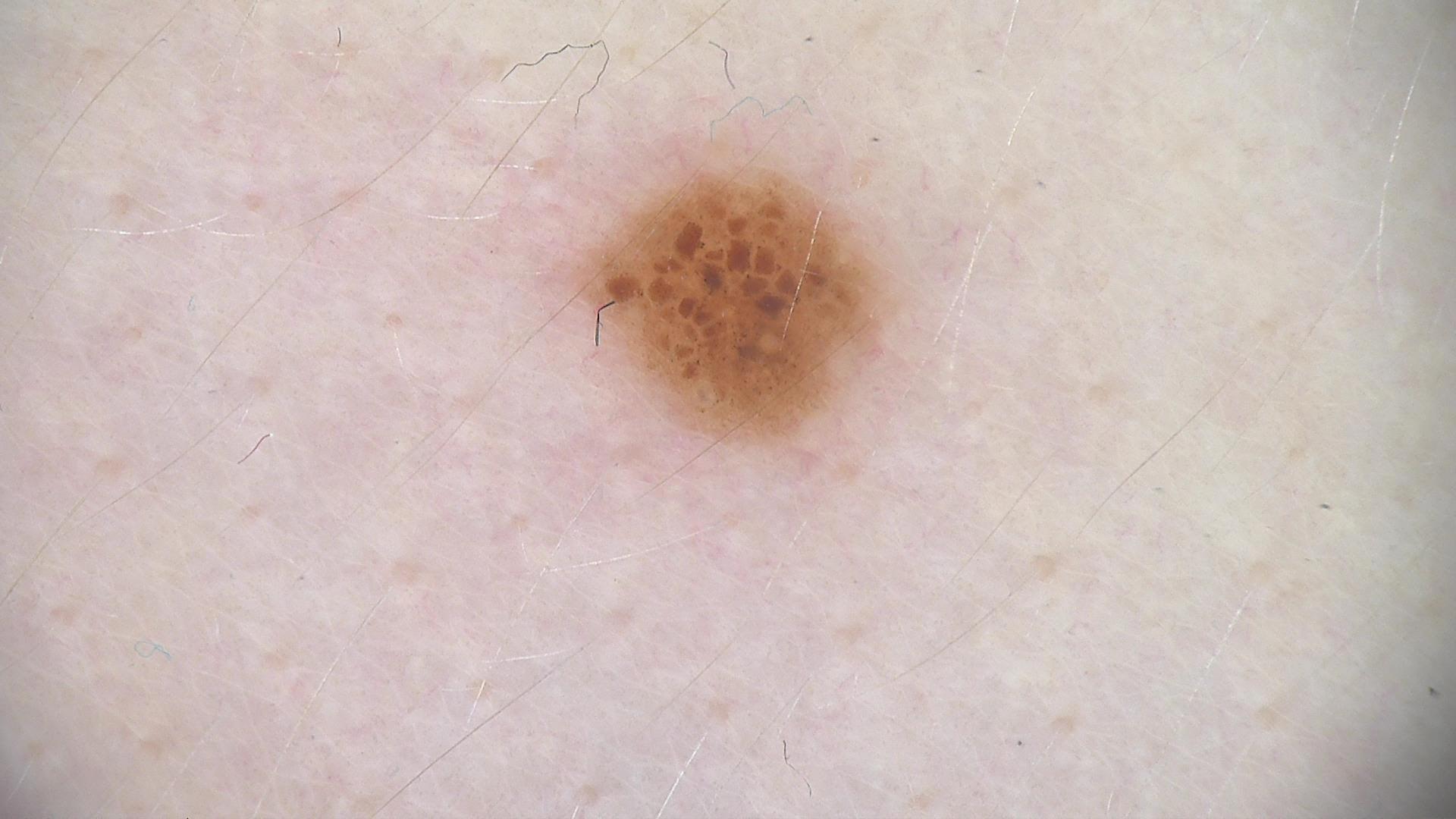A dermoscopic image of a skin lesion.
This is a banal lesion.
The diagnostic label was a compound nevus.